A dermoscopic image of a skin lesion.
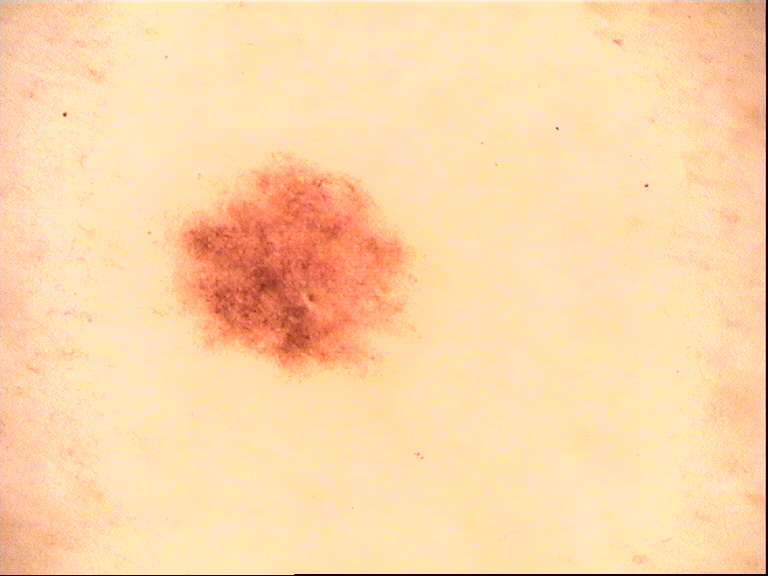Consistent with a benign lesion — a dysplastic junctional nevus.